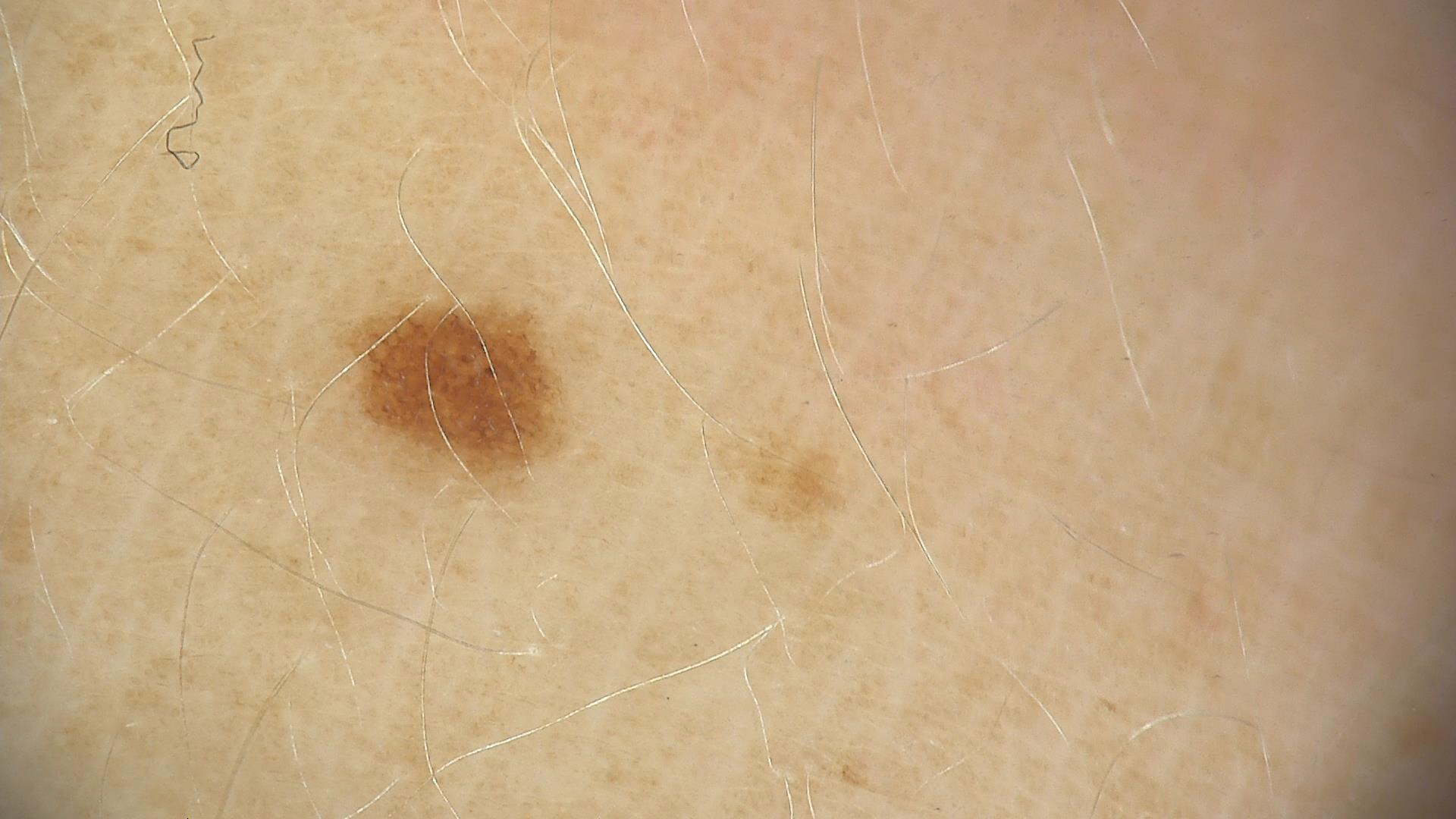The diagnostic label was a benign lesion — a dysplastic junctional nevus.